Fitzpatrick phototype II; non-clinician graders estimated MST 2–3. Symptoms reported: darkening, bothersome appearance and enlargement. The condition has been present for less than one week. The patient indicates the lesion is rough or flaky. An image taken at an angle. The lesion involves the head or neck.
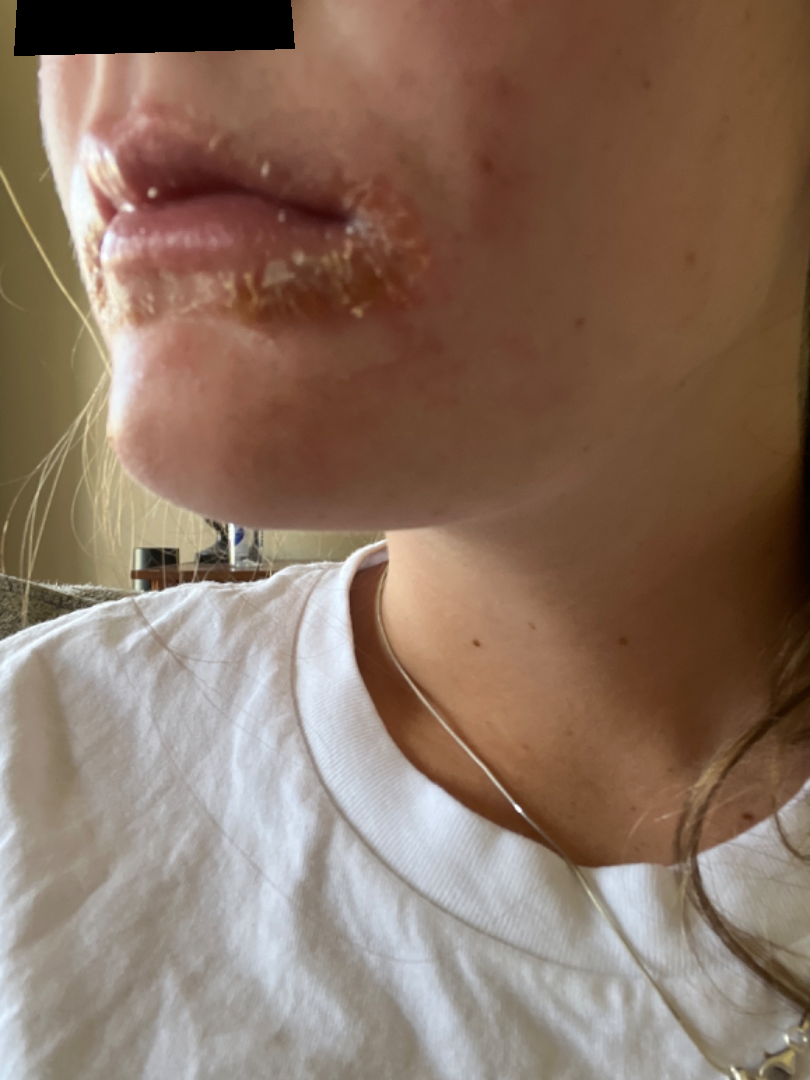Assessment:
Impetigo (weight 1.00).